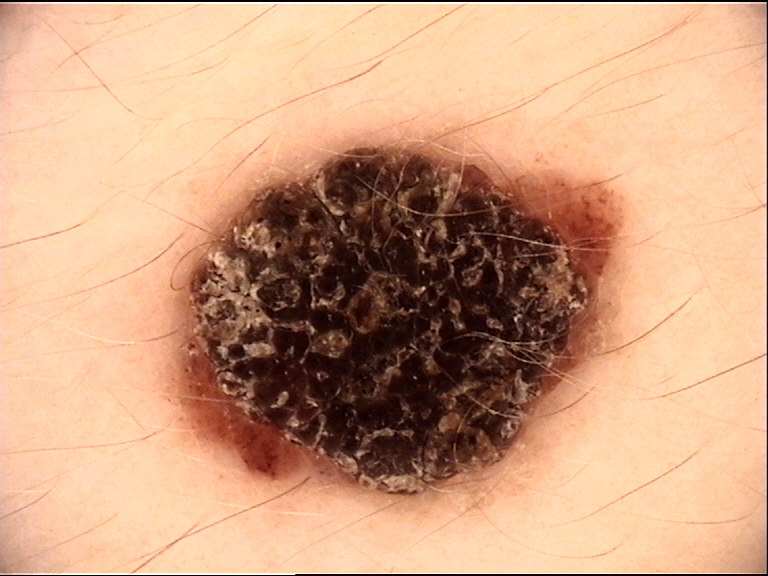Classified as a congenital compound nevus.